Close-up view · female contributor, age 40–49 · the patient indicates itching · the back of the hand is involved · texture is reported as raised or bumpy — 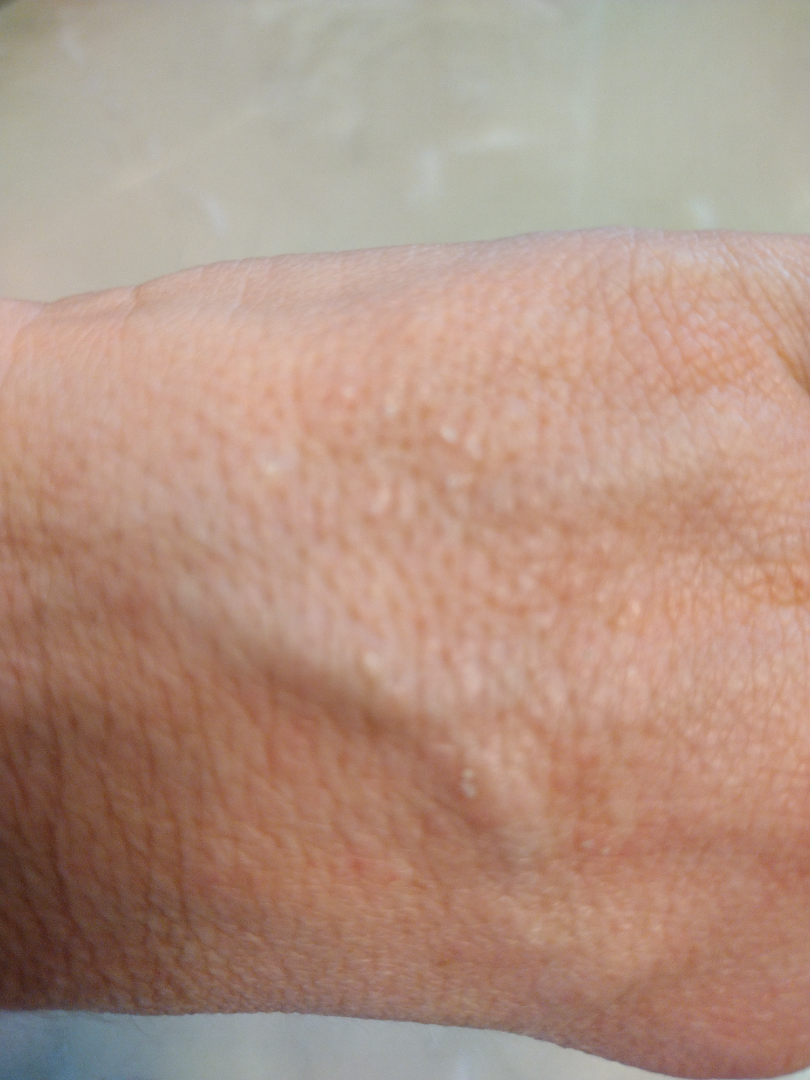* impression · reviewed remotely by three dermatologists: the differential includes Psoriasis and Eczema, with no clear leading consideration